Dermoscopy of a skin lesion.
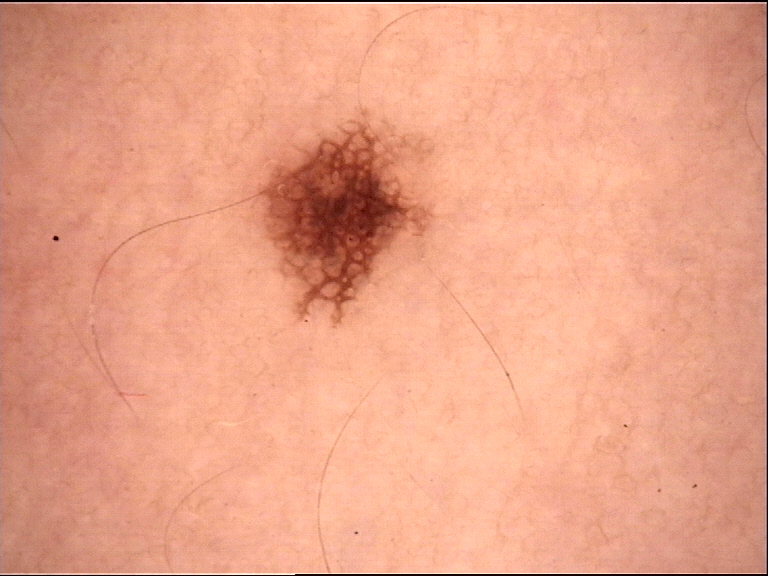- label · dysplastic junctional nevus (expert consensus)